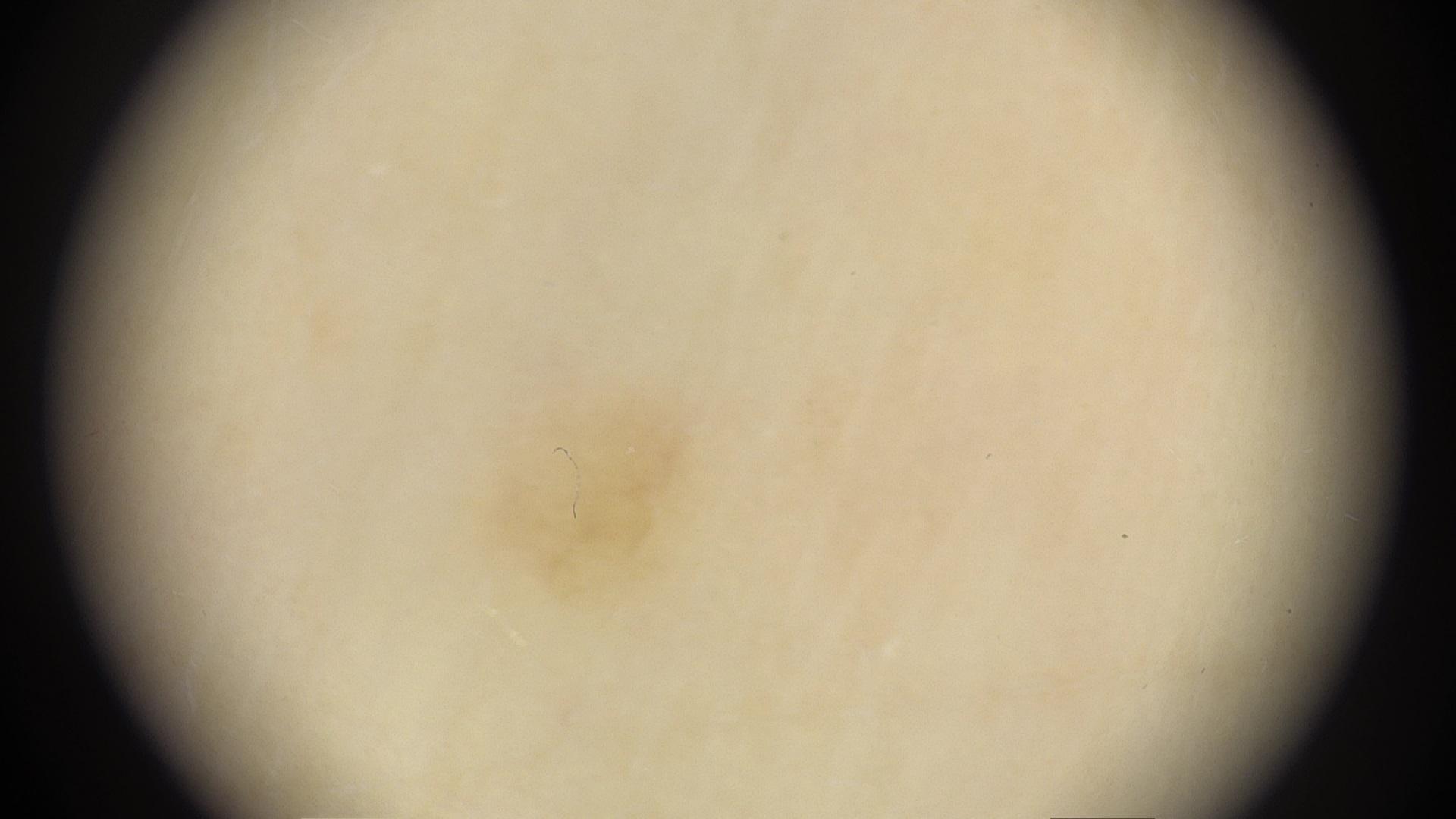<skin_lesion>
<skin_type>II</skin_type>
<image>contact-polarized dermoscopy</image>
<diagnosis>
<name>Solar lentigo</name>
<malignancy>benign</malignancy>
<confirmation>expert clinical impression</confirmation>
<lineage>epidermal</lineage>
</diagnosis>
</skin_lesion>